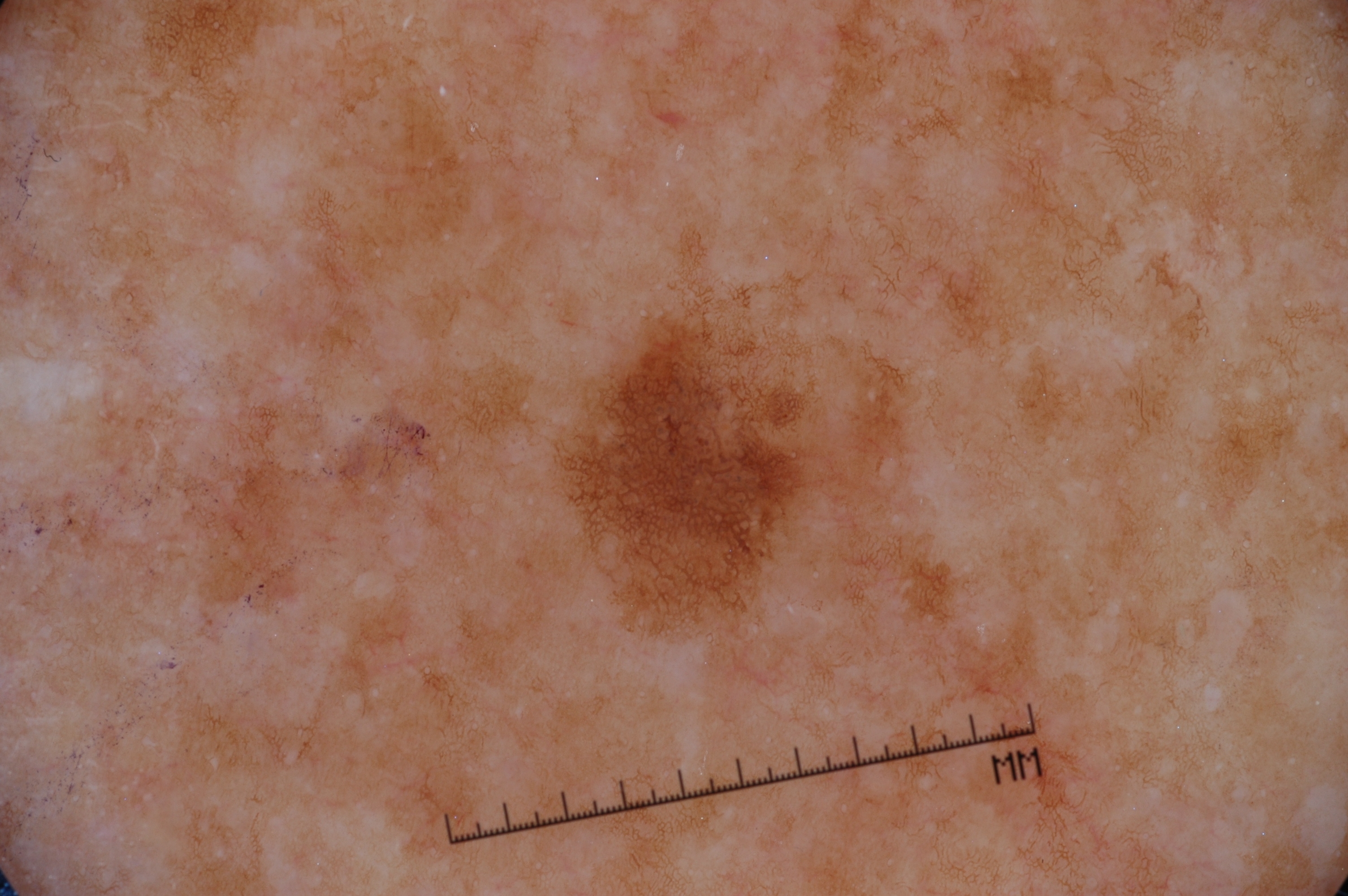subject: female, about 50 years old
modality: dermatoscopic image of a skin lesion
extent: ~8% of the field
lesion bbox: box(548, 219, 857, 646)
dermoscopic pattern: pigment network
assessment: a melanocytic nevus, a benign lesion